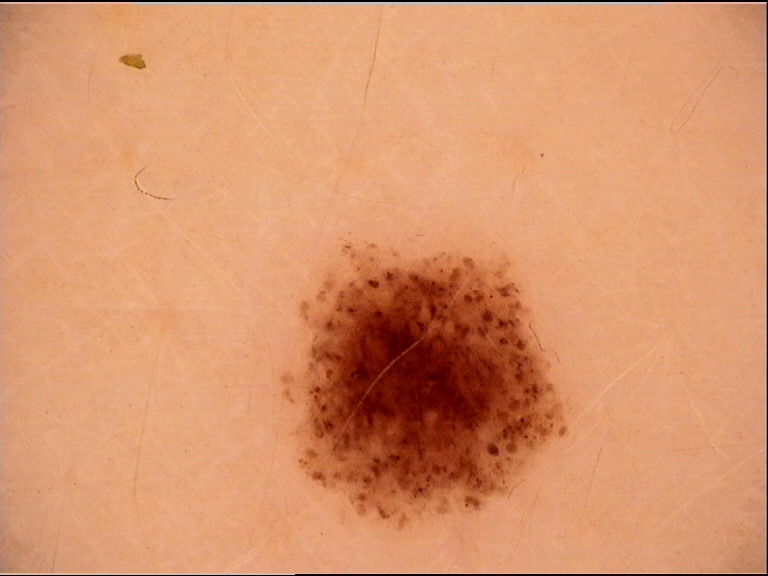imaging = dermatoscopy
label = junctional nevus (expert consensus)